Close-up view:
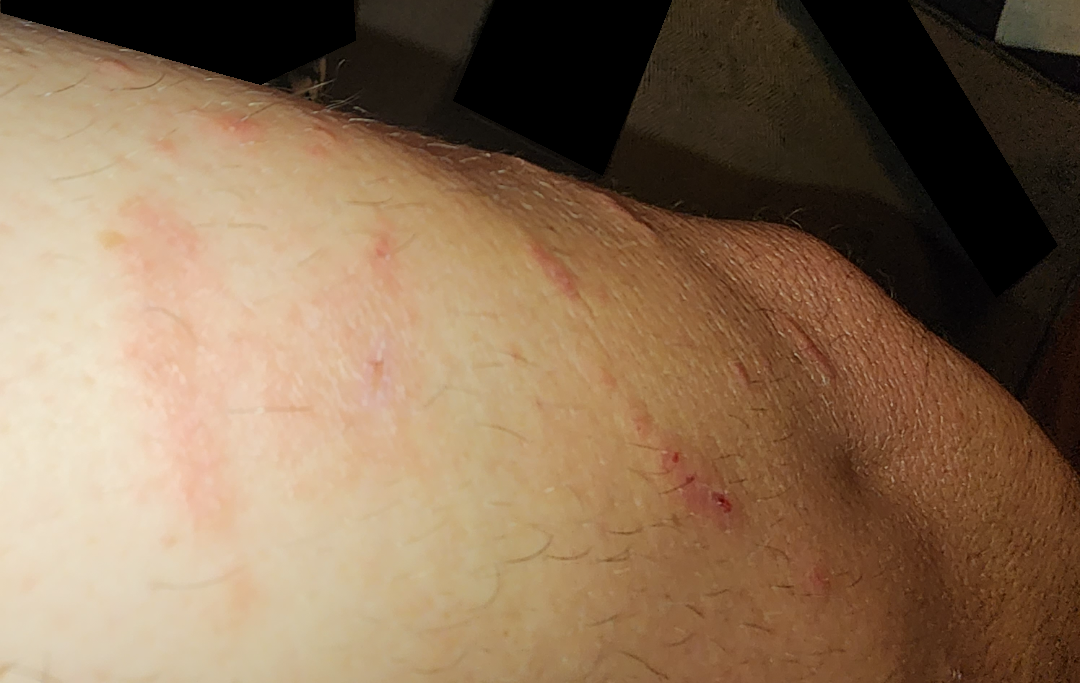Review: The case was indeterminate on photographic review.